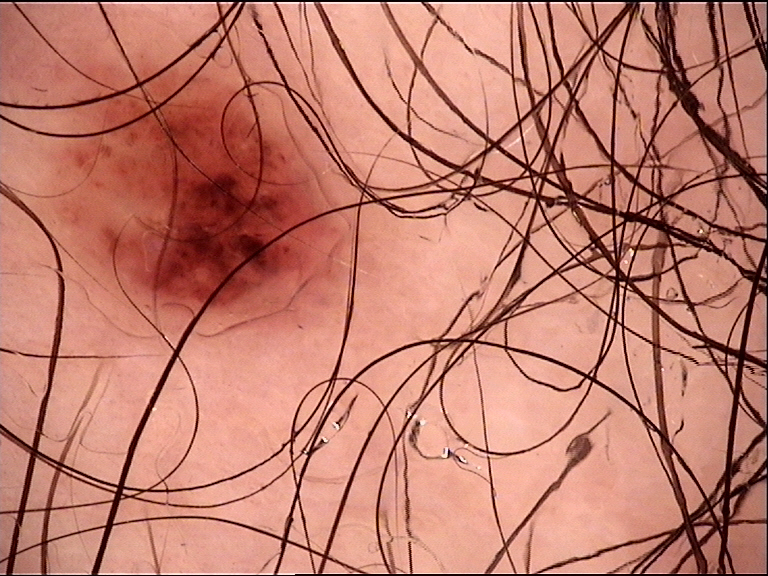Labeled as a compound nevus.